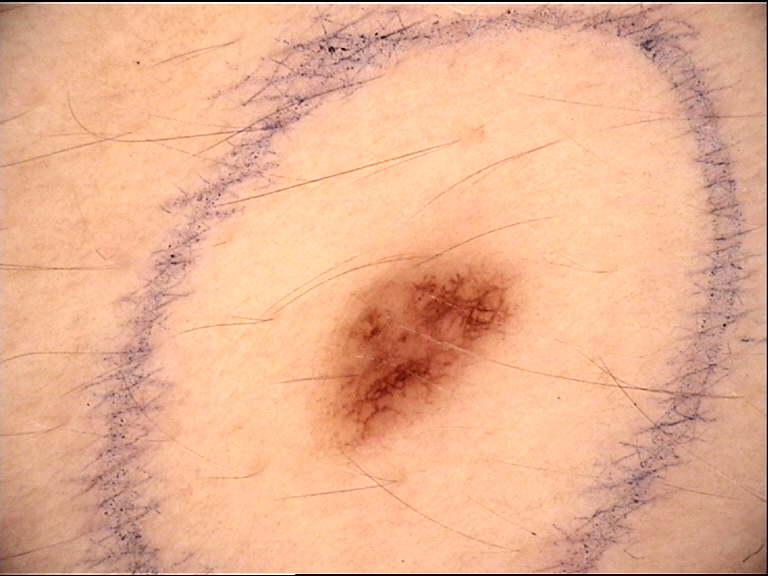A dermatoscopic image of a skin lesion. Classified as a benign lesion — a dysplastic junctional nevus.